No associated systemic symptoms reported · texture is reported as raised or bumpy · the condition has been present for less than one week · the leg is involved · the photograph is a close-up of the affected area · reported lesion symptoms include enlargement and itching · the patient described the issue as a rash:
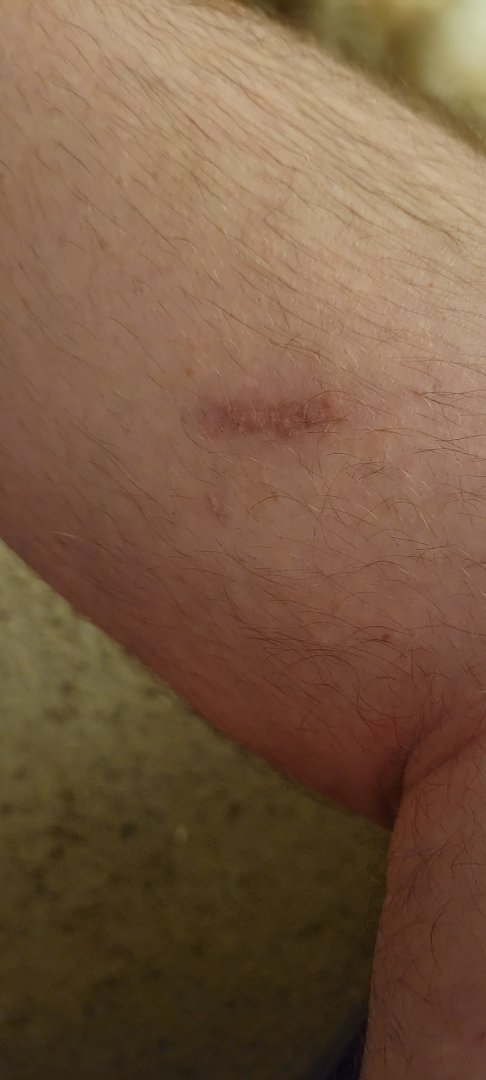Assessment:
The dermatologist could not determine a likely condition from the photograph alone.